A skin lesion imaged with contact-polarized dermoscopy · a male patient aged 38-42 · Fitzpatrick III:
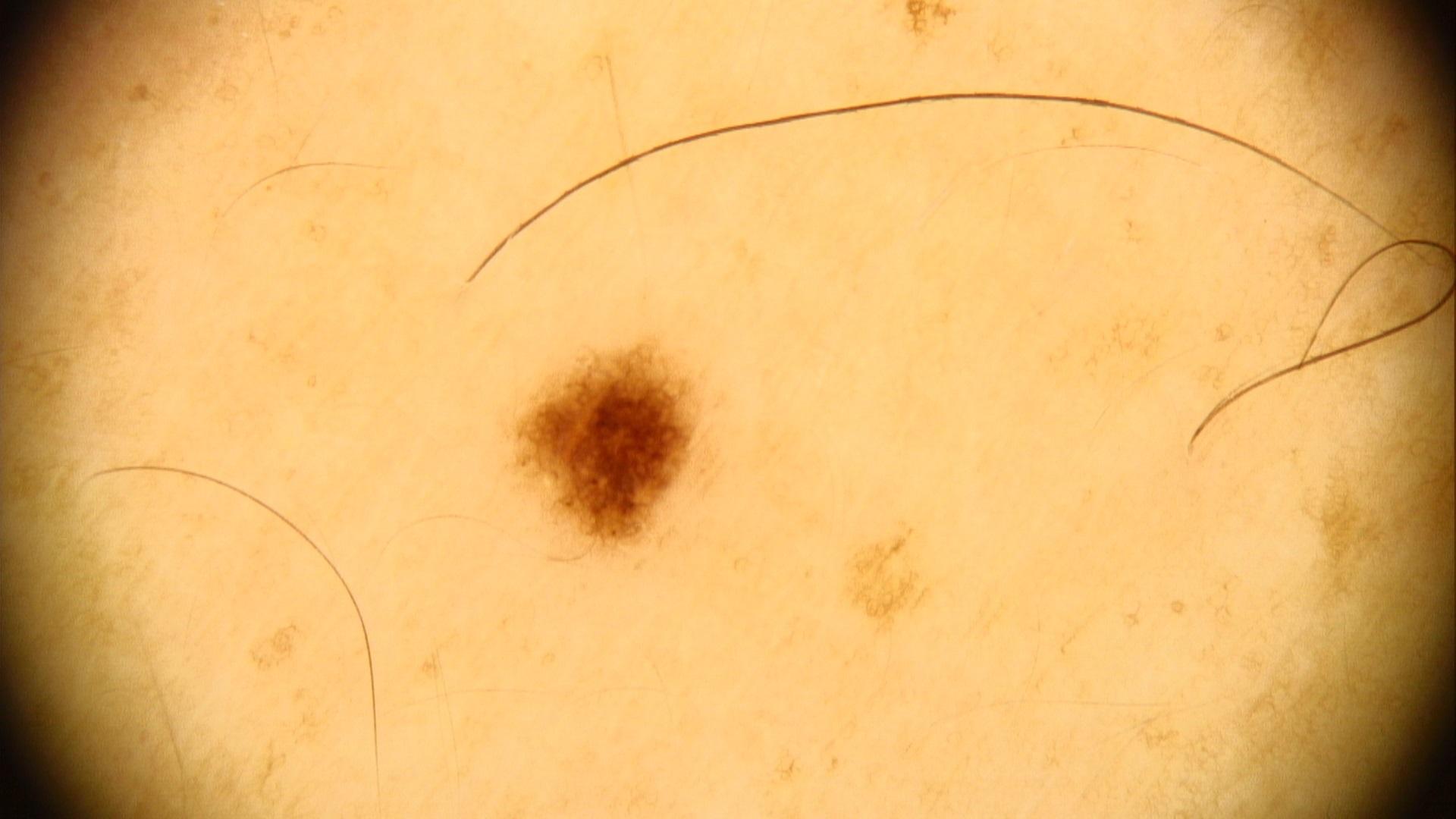Located on the trunk (the posterior trunk). Expert review favored a nevus.